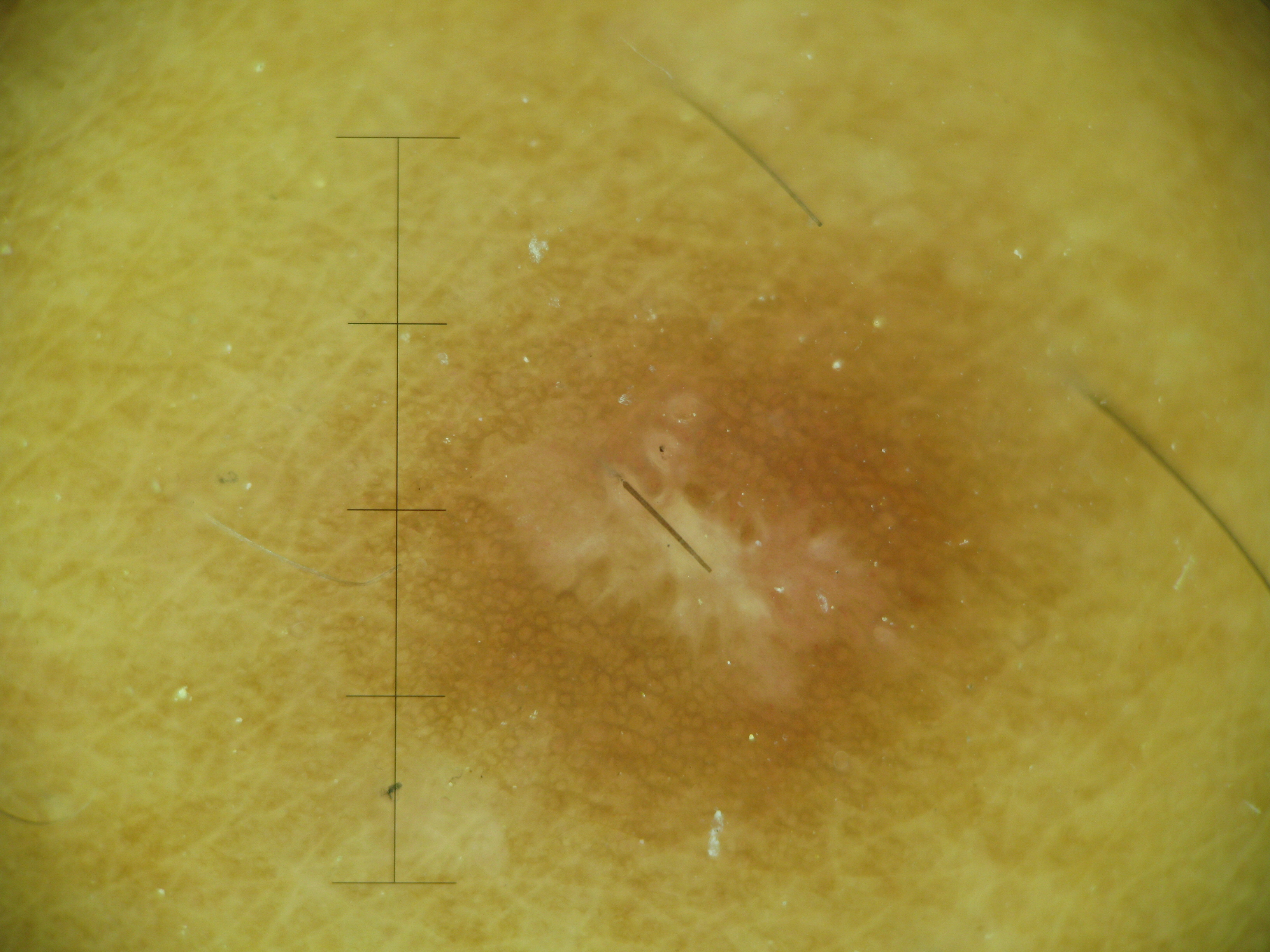Conclusion:
Labeled as a dermatofibroma.